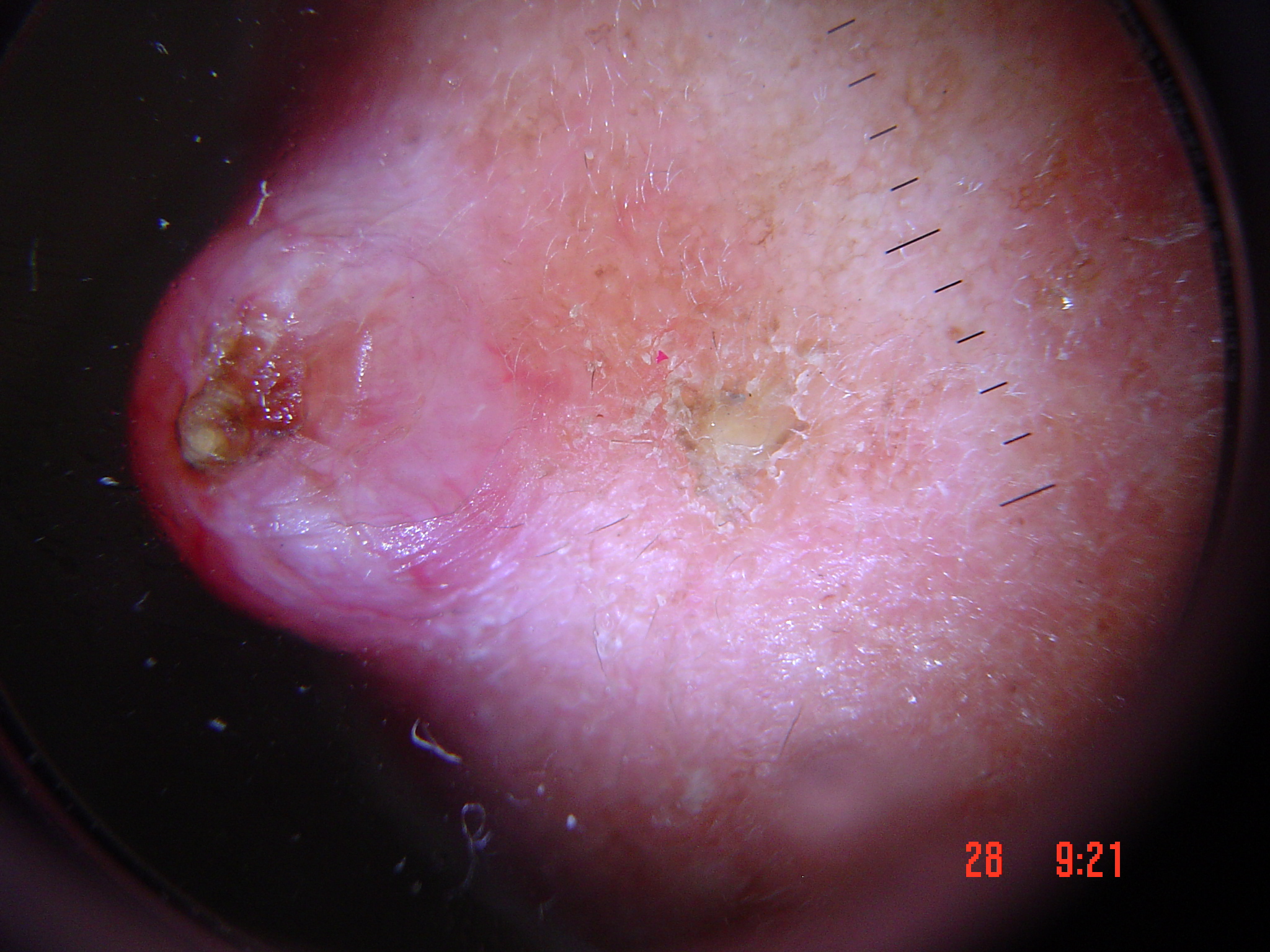A dermoscopic image of a skin lesion. The biopsy diagnosis was a keratinocytic lesion — a basal cell carcinoma.